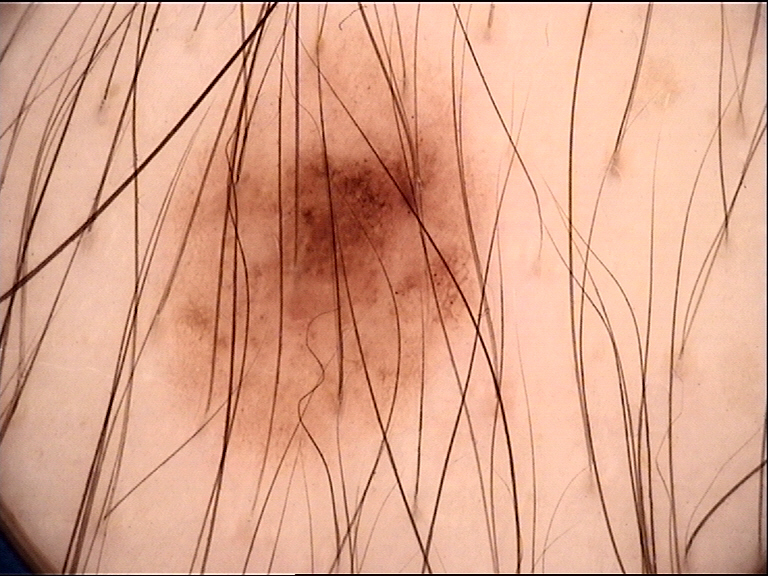label=dysplastic junctional nevus (expert consensus).